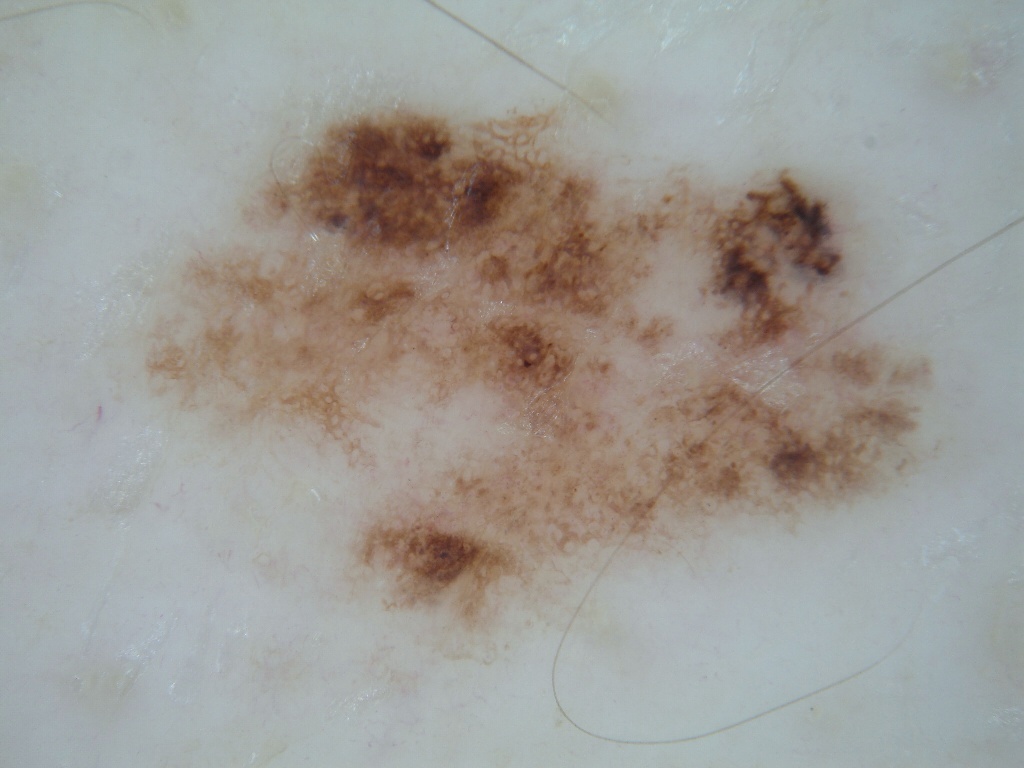Summary:
A male patient, aged approximately 80. A dermoscopic view of a skin lesion. The dermoscopic pattern shows pigment network. The lesion is located at (101, 77, 965, 693).
Impression:
The clinical diagnosis was a melanocytic nevus, a benign skin lesion.